A dermoscopic image of a skin lesion.
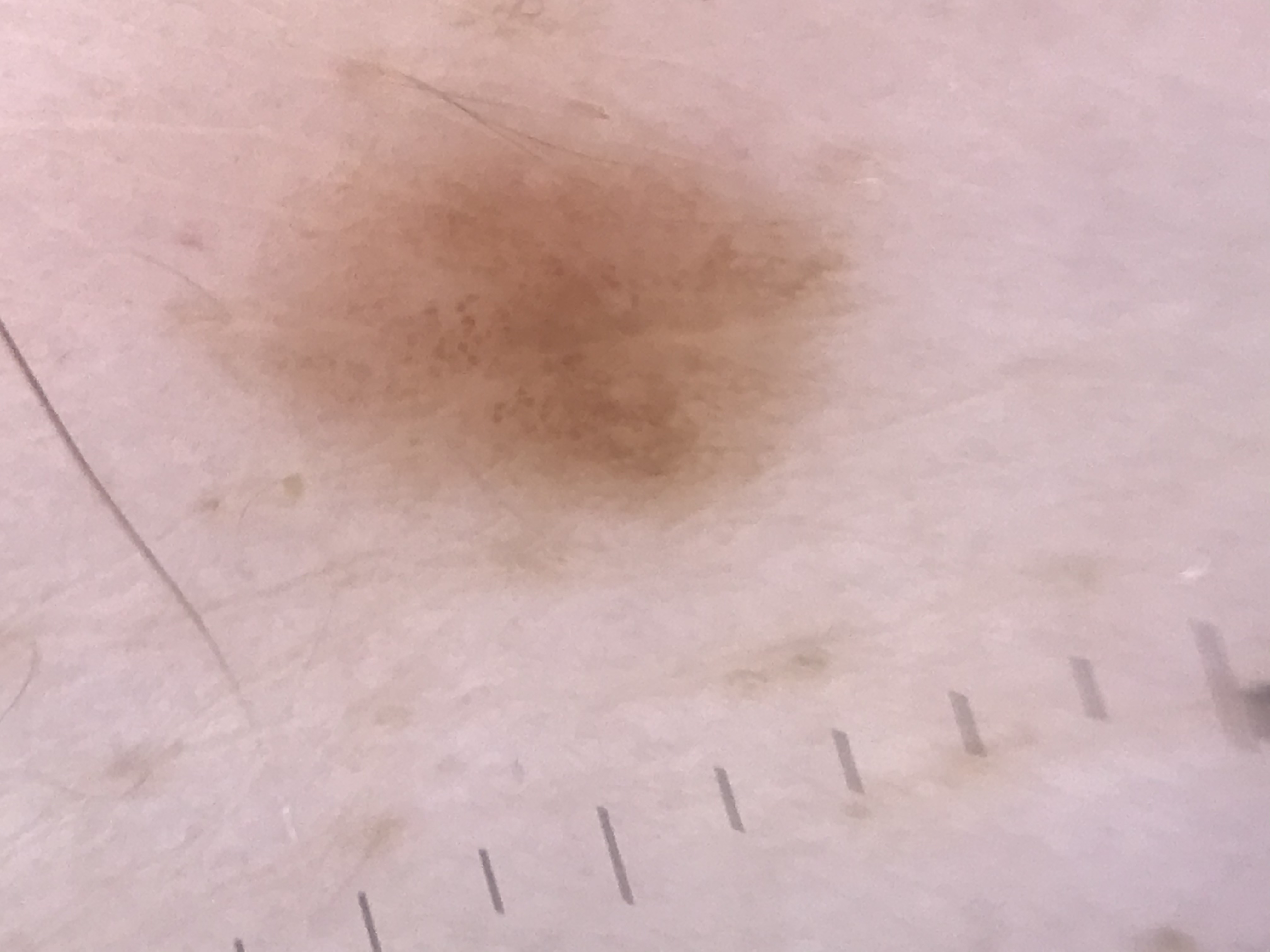• class — dysplastic junctional nevus (expert consensus)